This is a dermoscopic photograph of a skin lesion. A male patient aged 13-17: 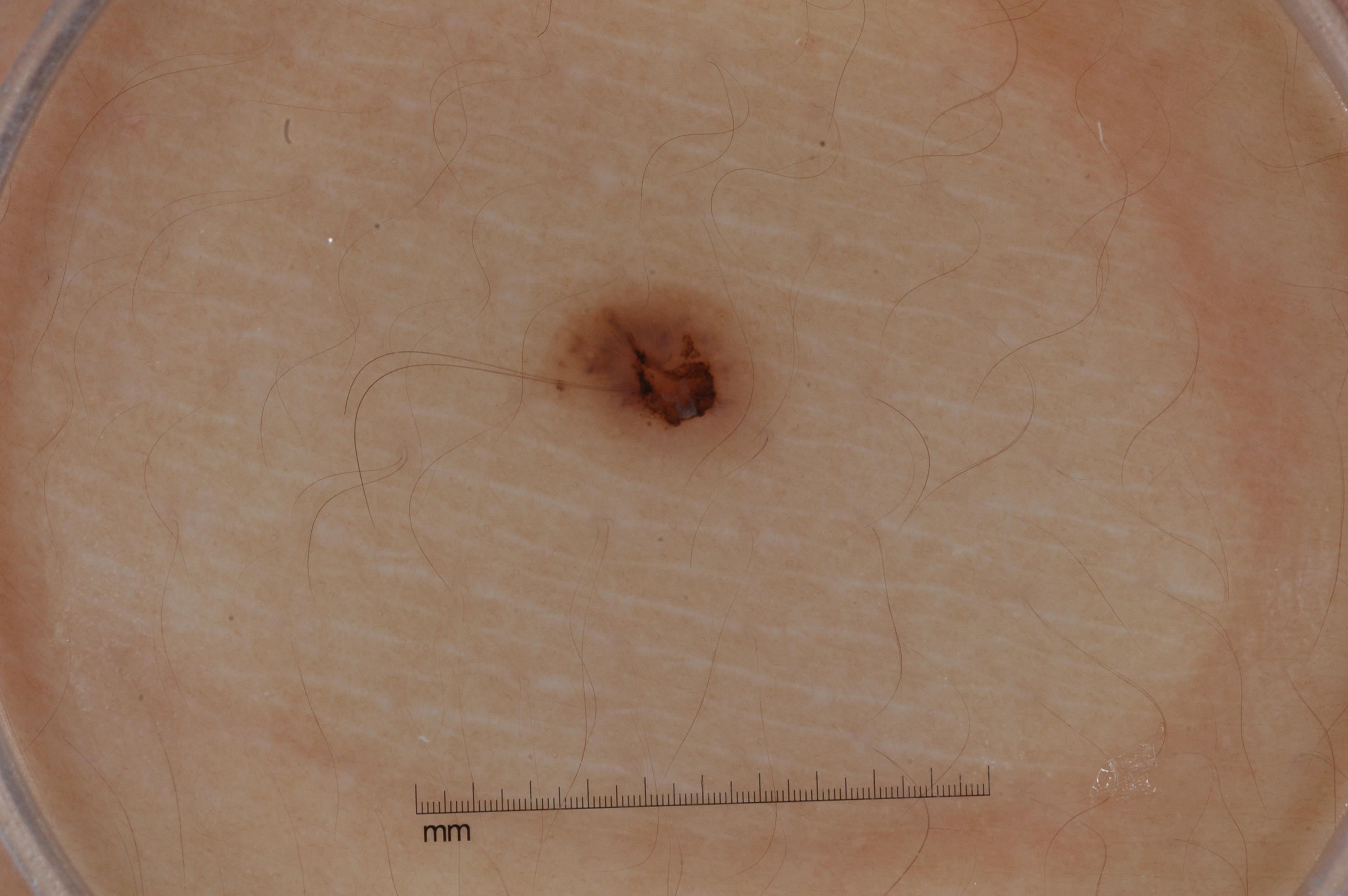Q: Where is the lesion in the image?
A: box(527, 280, 779, 469)
Q: Which dermoscopic features are absent?
A: streaks, milia-like cysts, pigment network, and negative network
Q: What is this lesion?
A: a melanocytic nevus